The chart notes no first-degree relative with melanoma and no prior melanoma. A female patient in their mid- to late 30s. The patient is Fitzpatrick phototype II — 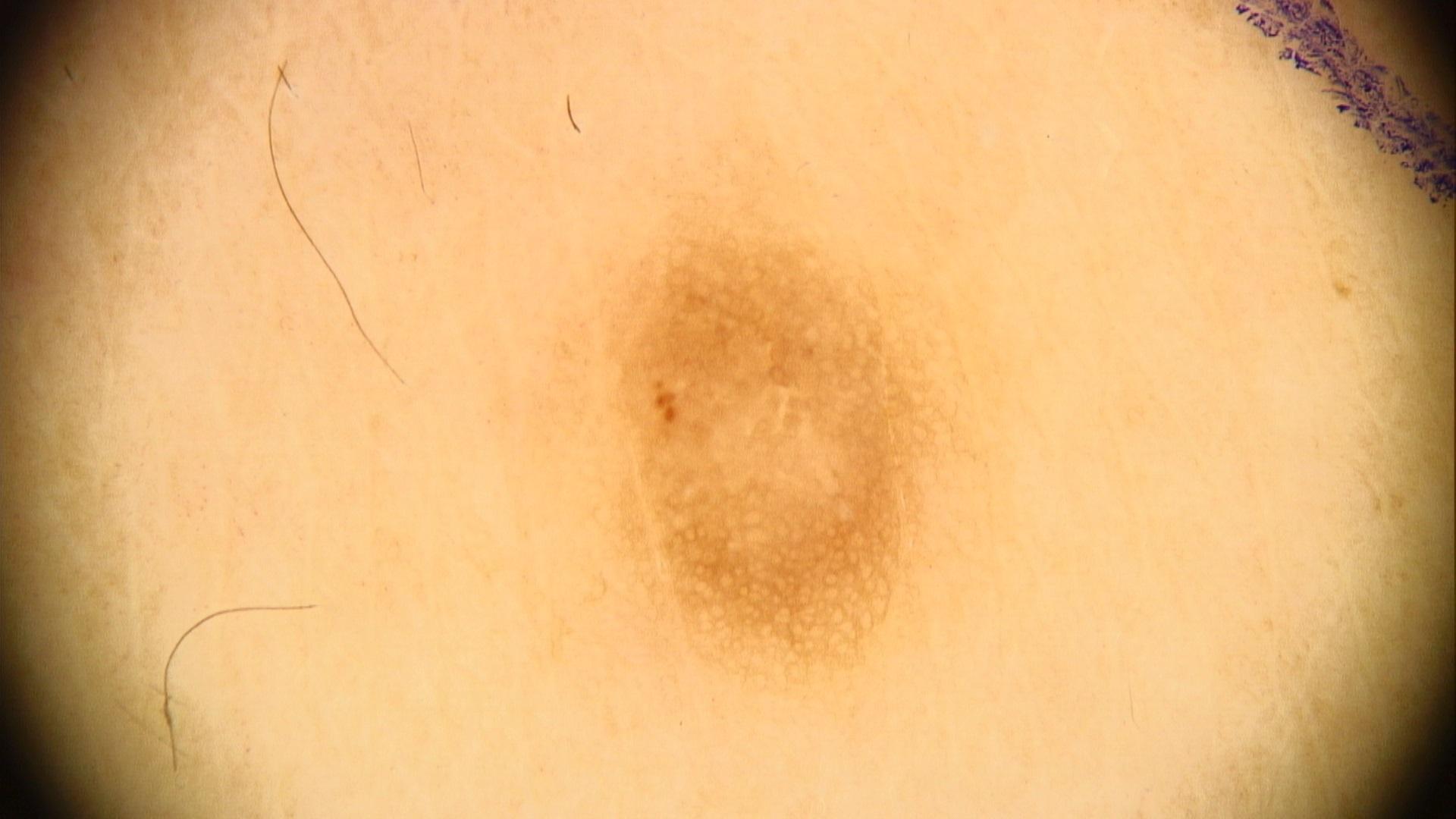diagnosis:
  name: Dermatofibroma
  malignancy: benign
  confirmation: expert clinical impression
  lineage: fibro-histiocytic